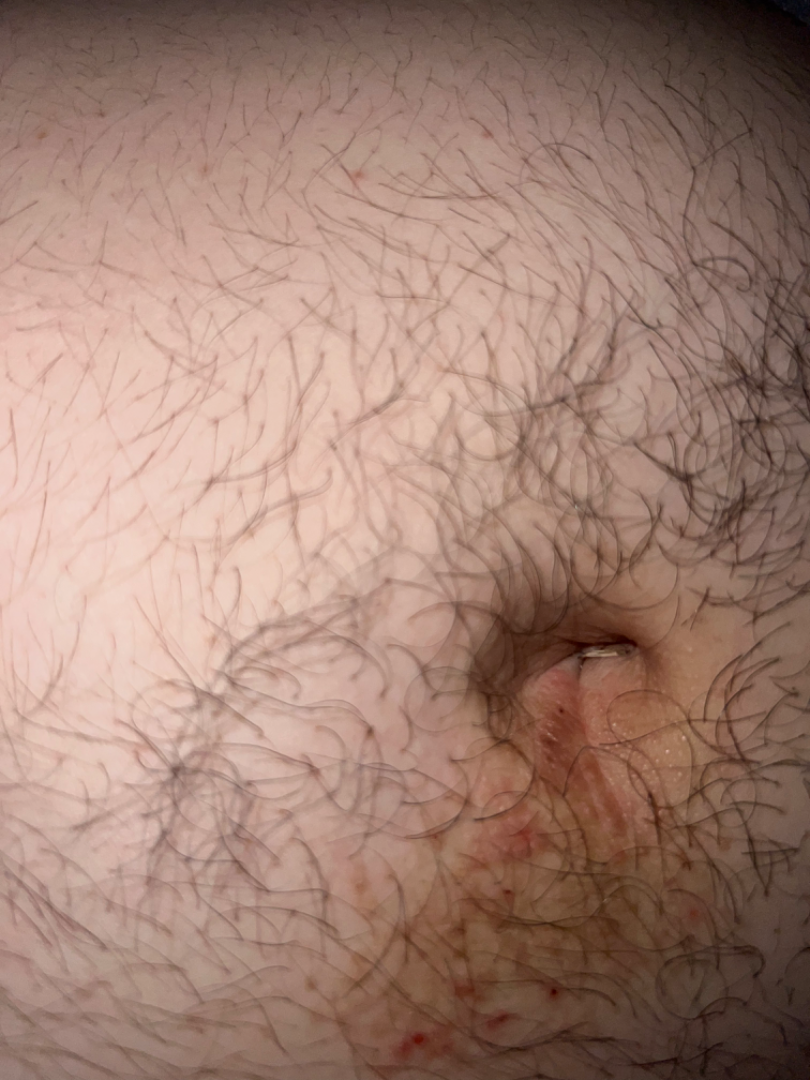| key | value |
|---|---|
| patient's own categorization | a rash |
| contributor | male, age 18–29 |
| shot type | close-up |
| skin tone | lay graders estimated Monk Skin Tone 2 |
| patient-reported symptoms | itching, darkening and bothersome appearance |
| lesion texture | raised or bumpy |
| duration | more than one year |
| impression | Contact dermatitis and Candidal intertrigo were each considered, in no particular order; a more distant consideration is Scabies; less likely is Dermatosis caused by lice |